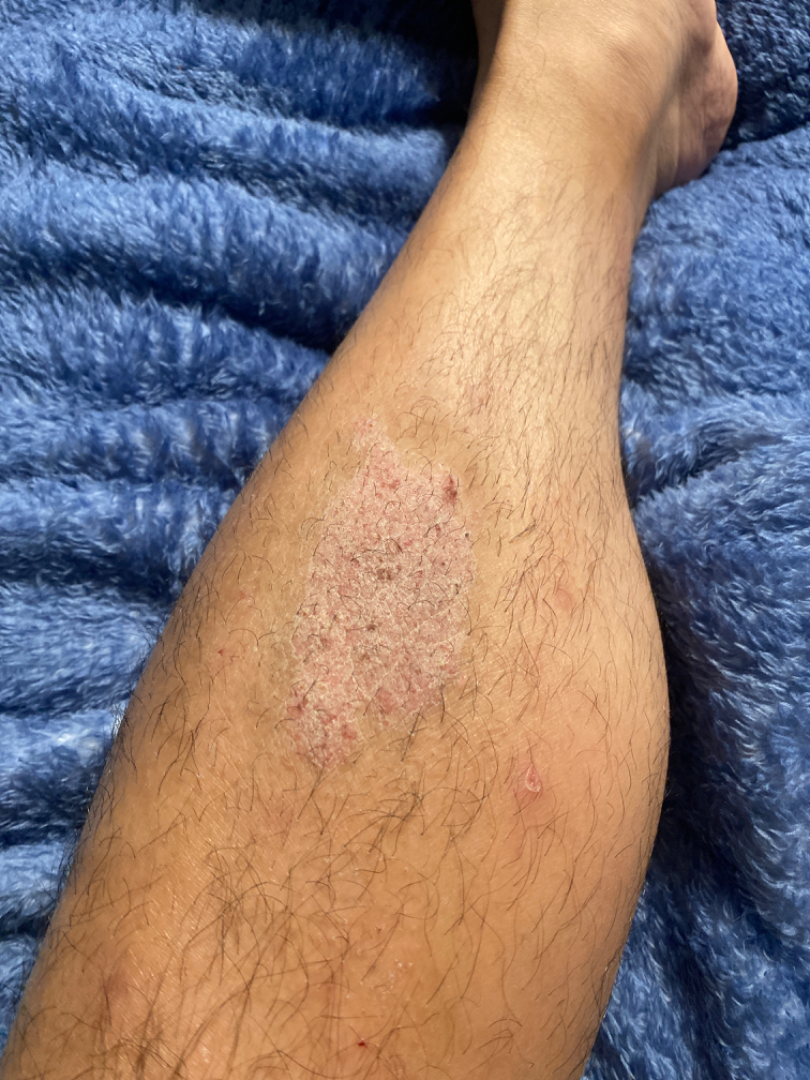Clinical context: The contributor notes the condition has been present for three to twelve months. The affected area is the leg. Texture is reported as rough or flaky. An image taken at a distance. Assessment: A single dermatologist reviewed the case: the differential is split between Lichen sclerosus and Psoriasis.